Male patient, age 18–29 · no associated systemic symptoms reported · the back of the torso, arm and head or neck are involved · the lesion is described as raised or bumpy · present for less than one week · symptoms reported: itching · skin tone: FST V; human graders estimated MST 6 (US pool) or 4 (India pool) · the patient considered this a rash · this is a close-up image:
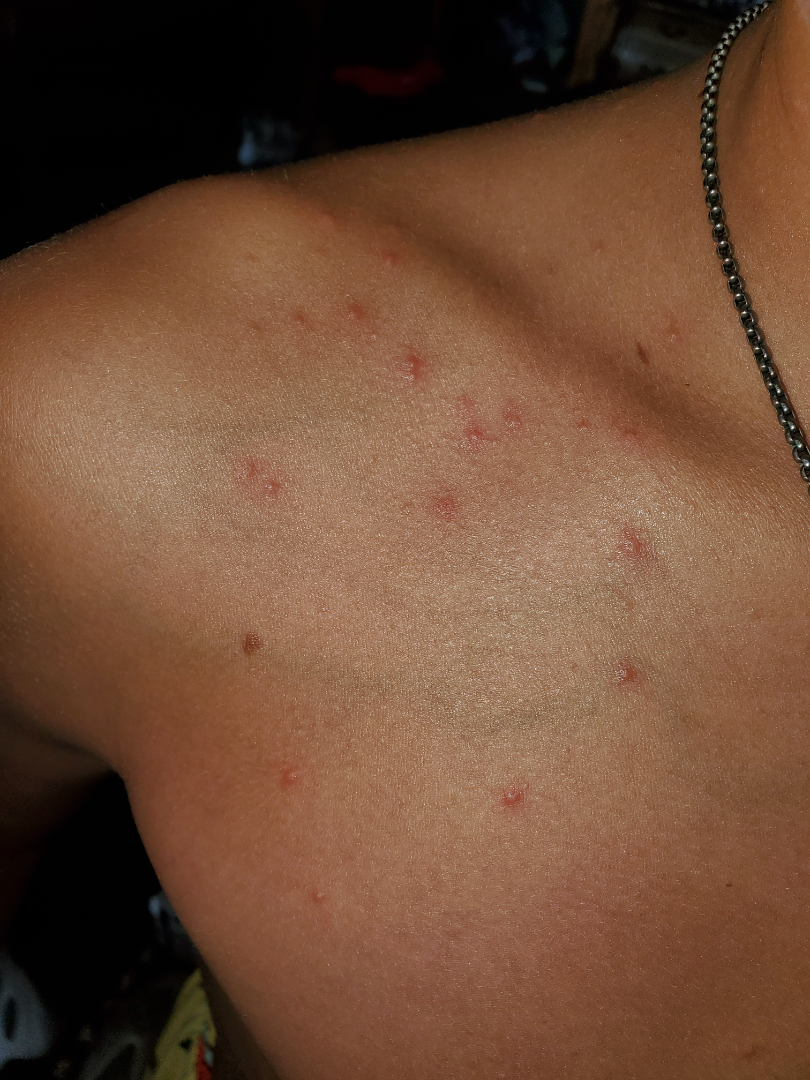On photographic review by a dermatologist, the reviewer's impression was Folliculitis.